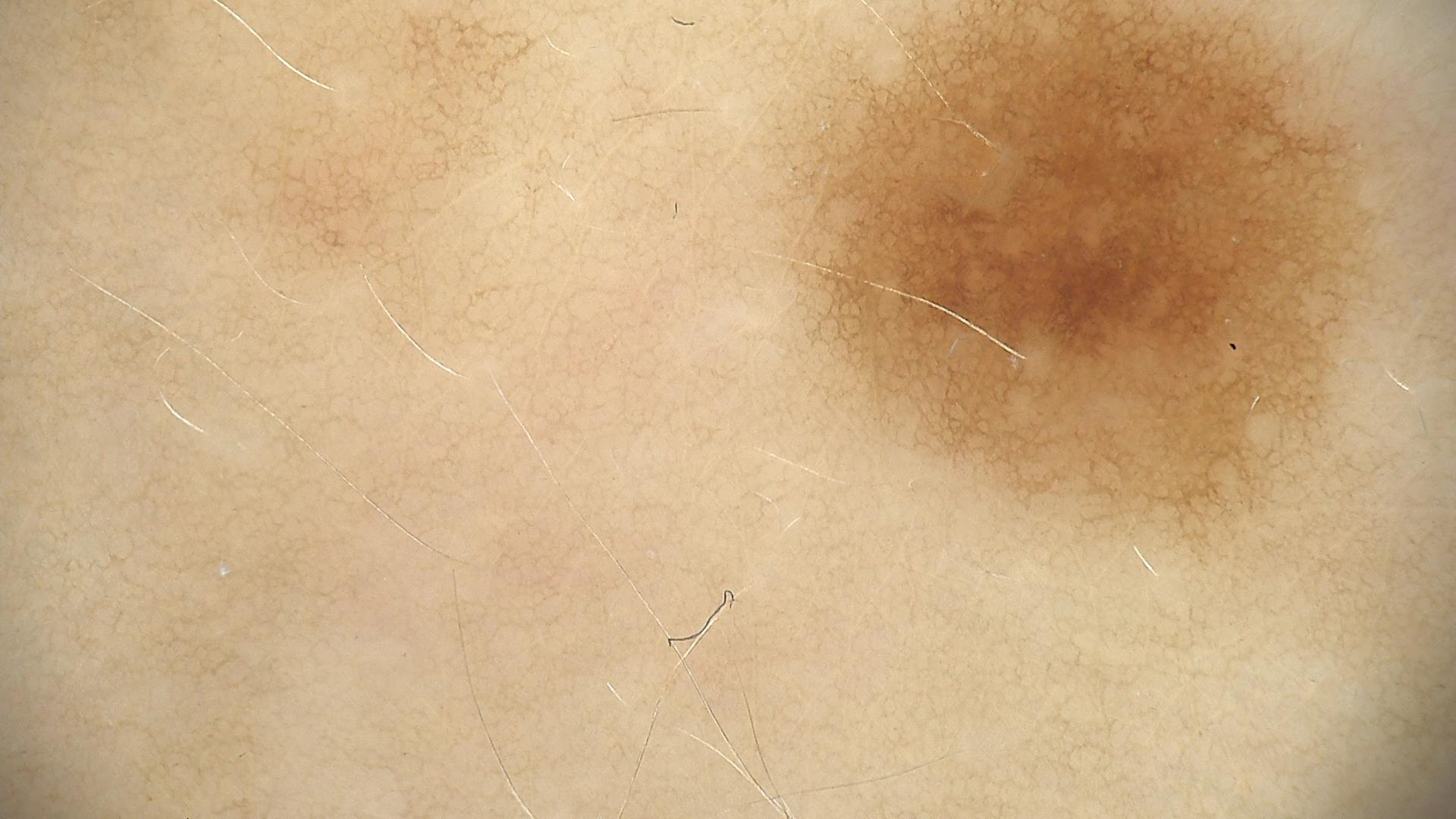Case:
A dermoscopic image of a skin lesion.
Impression:
Diagnosed as a dysplastic junctional nevus.